A female subject in their 80s. A smartphone photograph of a skin lesion. The patient is skin type II.
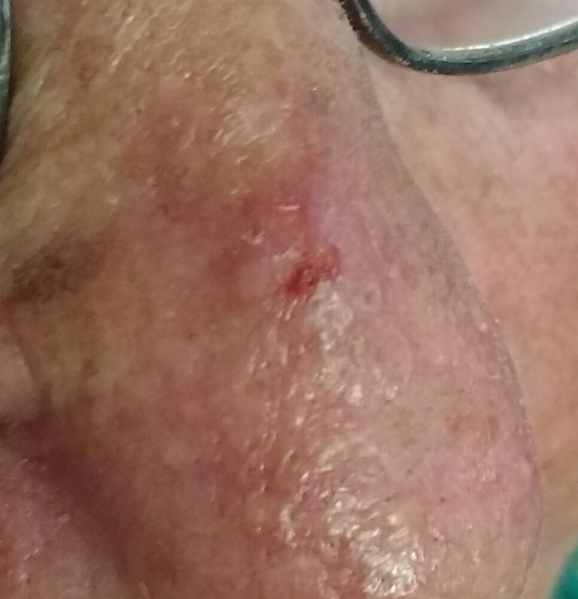{"lesion_location": "the nose", "symptoms": {"present": ["bleeding", "elevation"]}, "diagnosis": {"name": "basal cell carcinoma", "code": "BCC", "malignancy": "malignant", "confirmation": "histopathology"}}